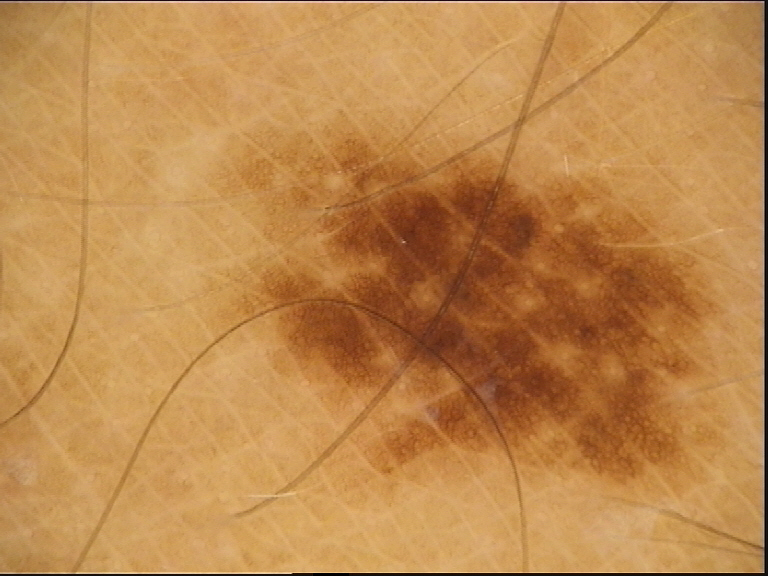Q: What is the imaging modality?
A: dermoscopy
Q: What is this lesion?
A: dysplastic junctional nevus (expert consensus)